A dermoscopic photograph of a skin lesion.
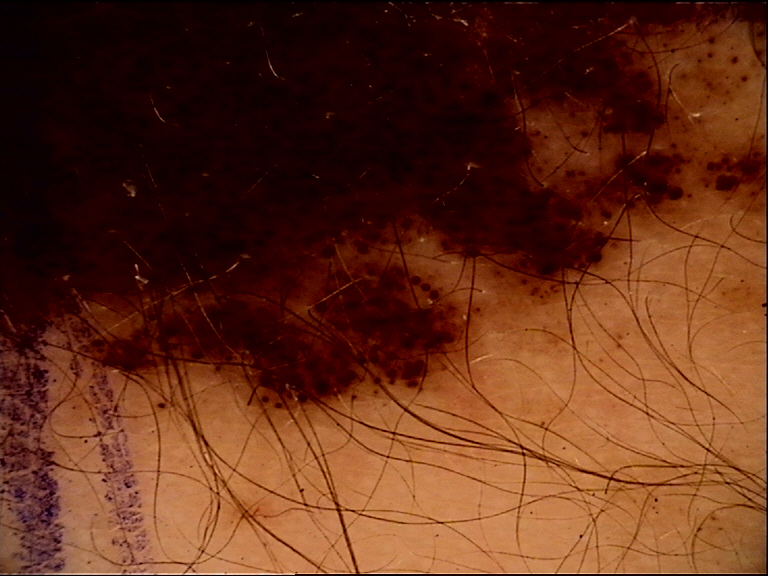| field | value |
|---|---|
| subtype | banal |
| class | congenital compound nevus (expert consensus) |